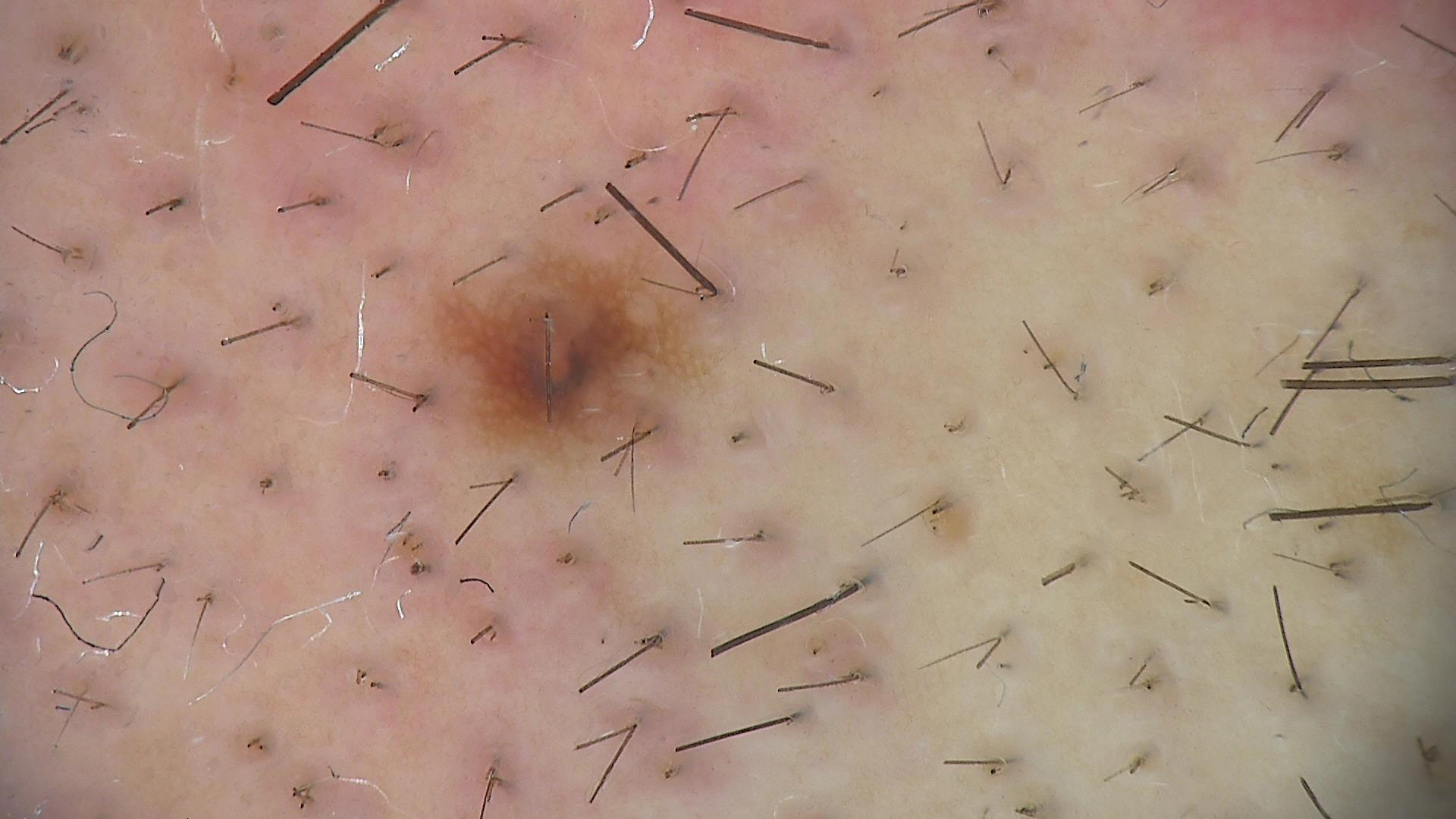Q: What is this lesion?
A: dysplastic junctional nevus (expert consensus)